A clinical photo of a skin lesion taken with a smartphone; a patient 77 years of age:
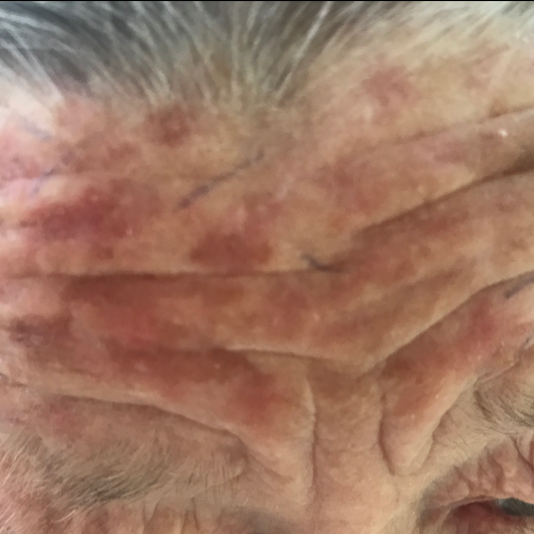<lesion>
<lesion_location>the face</lesion_location>
<symptoms>
<absent>change in appearance, itching</absent>
</symptoms>
<diagnosis>
<name>actinic keratosis</name>
<code>ACK</code>
<malignancy>indeterminate</malignancy>
<confirmation>clinical consensus</confirmation>
</diagnosis>
</lesion>